A female patient aged 83 or over · recorded as Fitzpatrick phototype II.
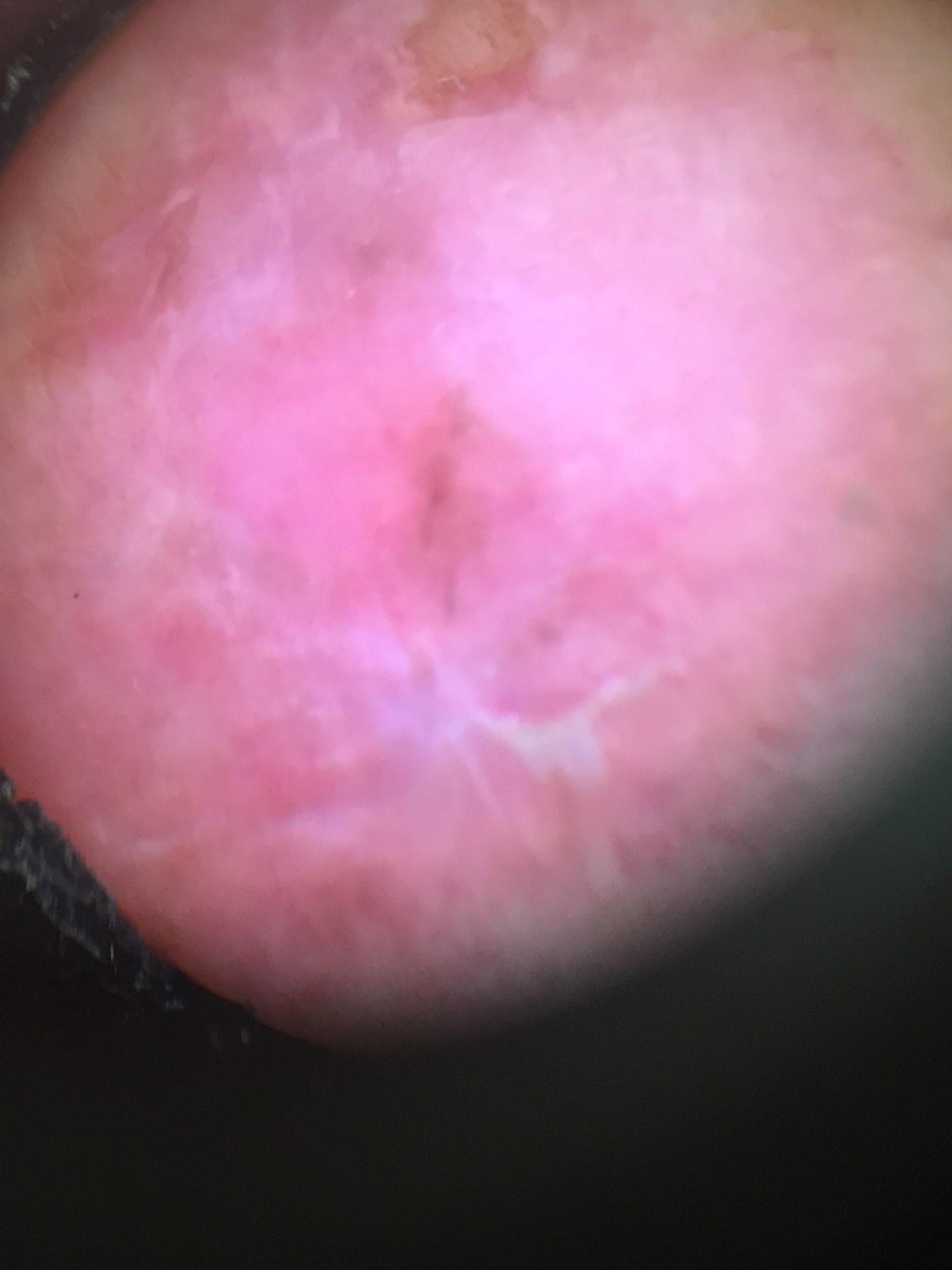Findings: The lesion was found on the head or neck. Conclusion: The biopsy diagnosis was a skin cancer — a squamous cell carcinoma.